Dermoscopy of a skin lesion: 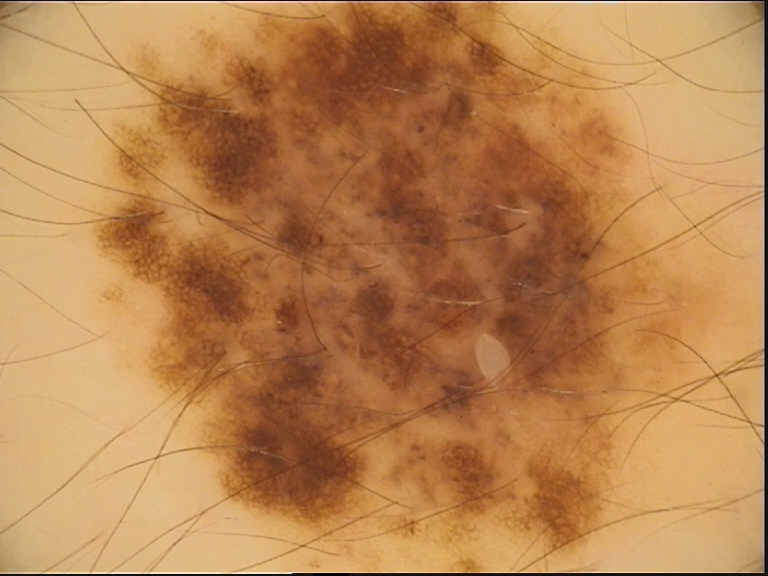<case>
  <diagnosis>
    <name>congenital dysplastic compound nevus</name>
    <code>ccd</code>
    <malignancy>benign</malignancy>
    <super_class>melanocytic</super_class>
    <confirmation>expert consensus</confirmation>
  </diagnosis>
</case>